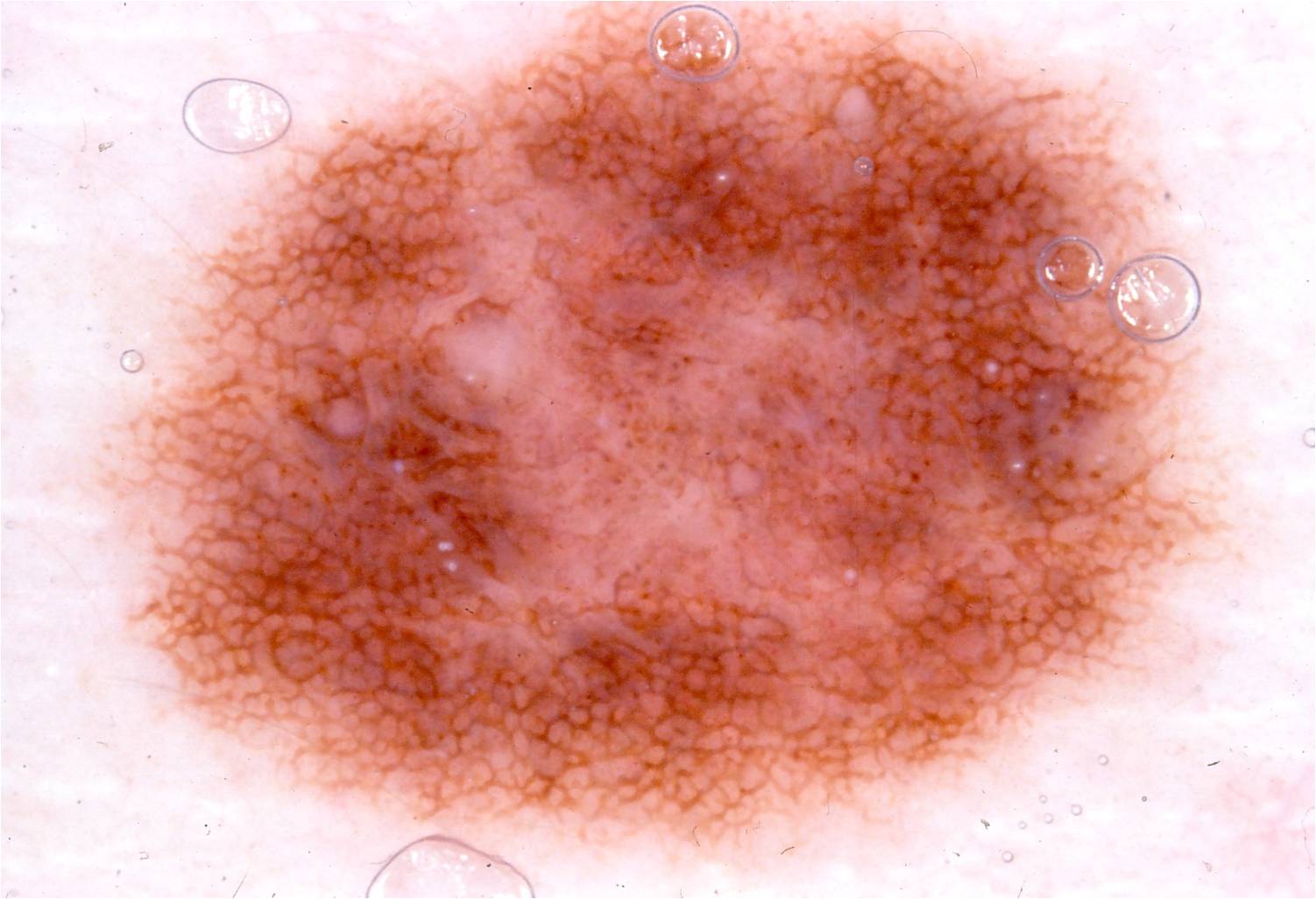Notes:
* image · dermoscopic image
* patient · male, aged 48 to 52
* location · x1=85, y1=1, x2=1263, y2=860
* dermoscopic findings · pigment network and globules
* extent · large
* diagnostic label · a melanocytic nevus